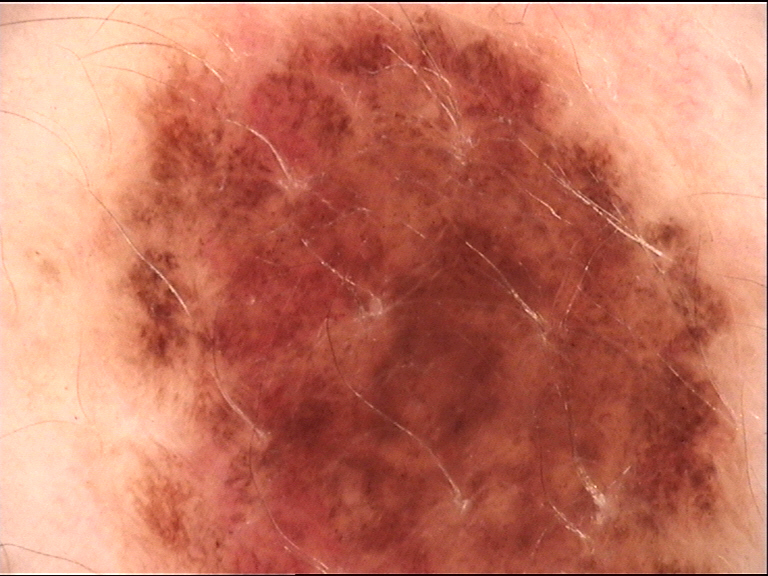- assessment · dysplastic junctional nevus (expert consensus)